The patient is a male in their 50s · a dermoscopic view of a skin lesion: 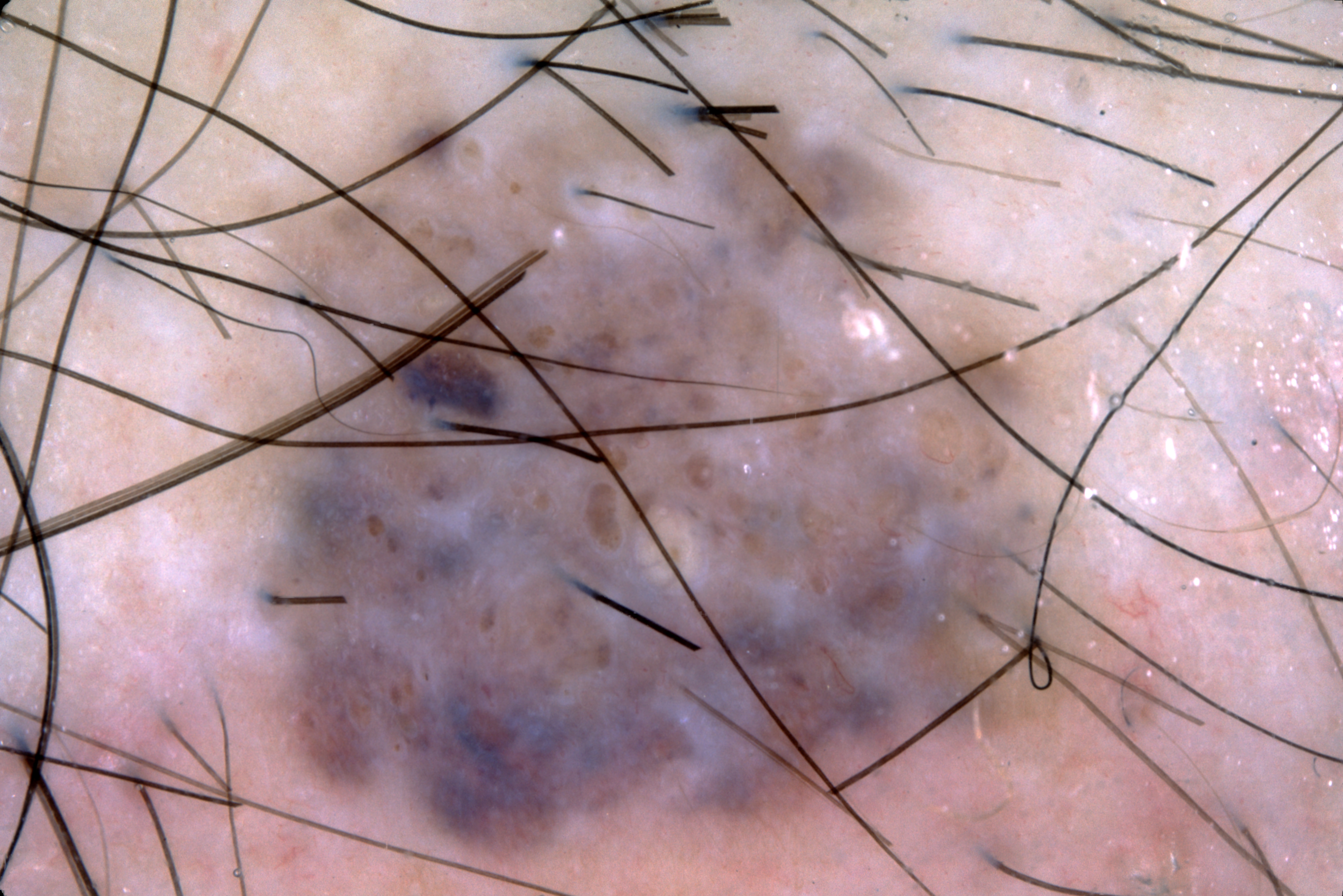dermoscopic pattern=milia-like cysts
lesion bbox=126, 31, 1186, 887
diagnostic label=a melanocytic nevus, a benign skin lesion